The affected area is the arm and leg; the photo was captured at a distance: 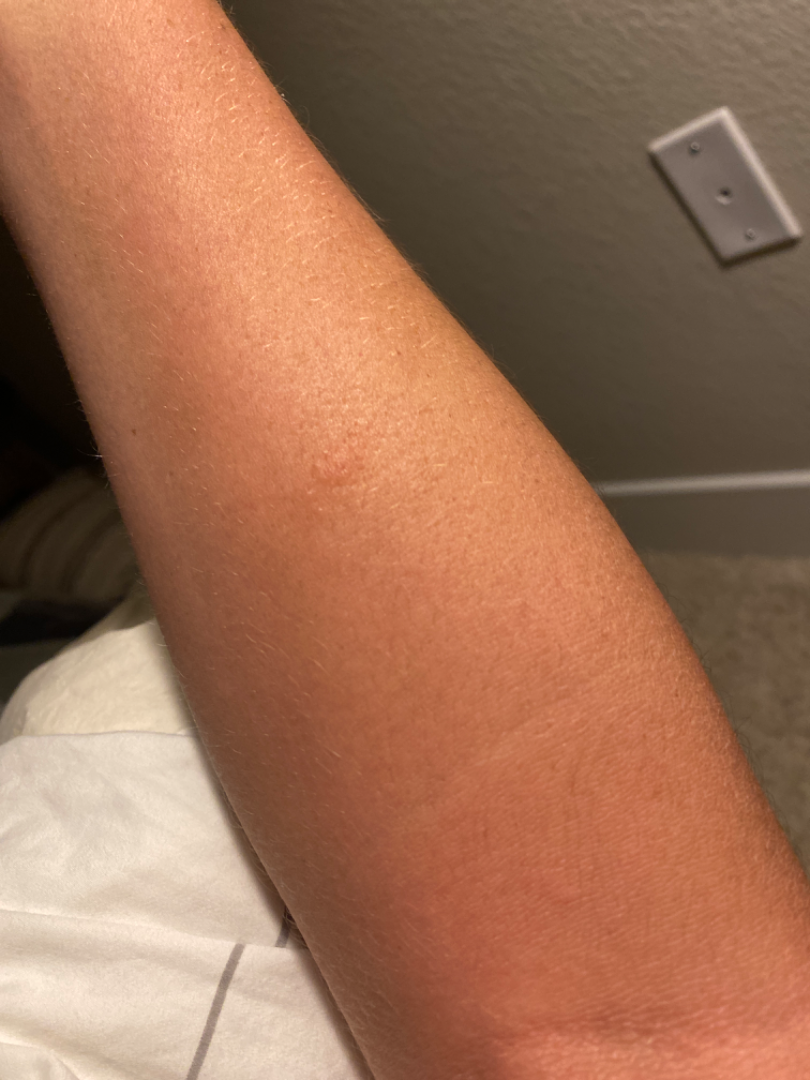Findings:
Diagnostic features were not clearly distinguishable in this photograph.
Background:
The condition has been present for less than one week. The lesion is described as rough or flaky and raised or bumpy.